Located on the leg. An image taken at a distance:
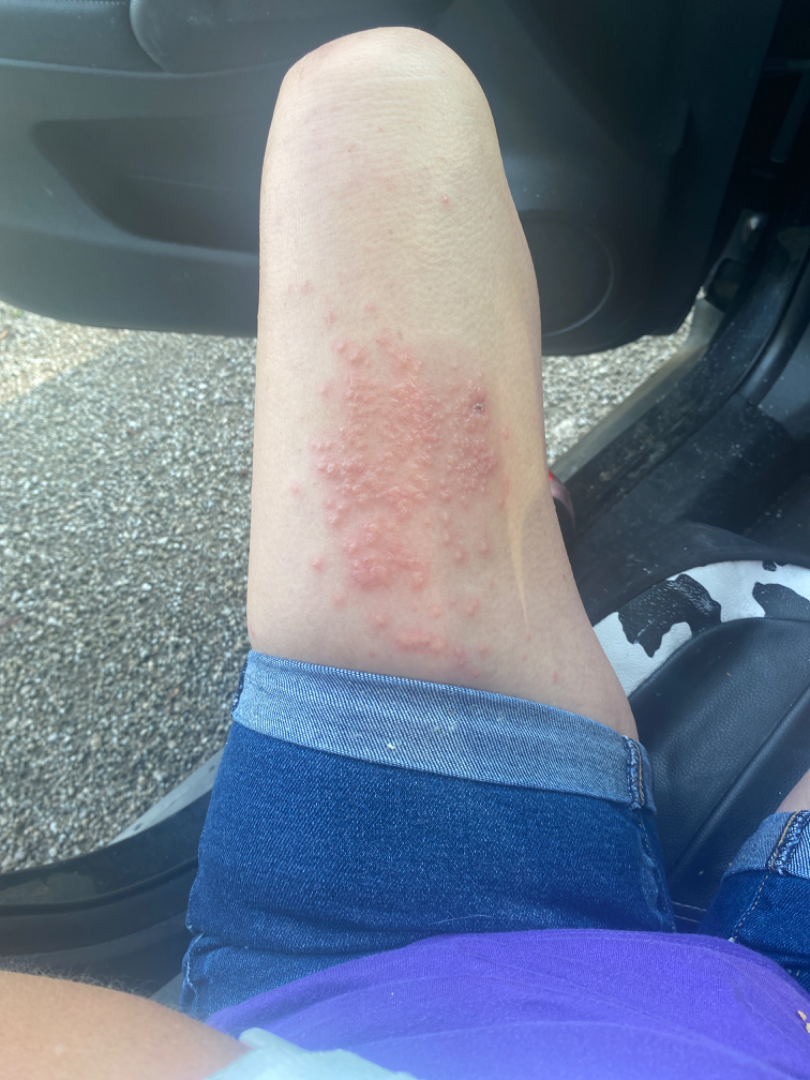The case was difficult to assess from the available photograph.